A skin lesion imaged with a dermatoscope:
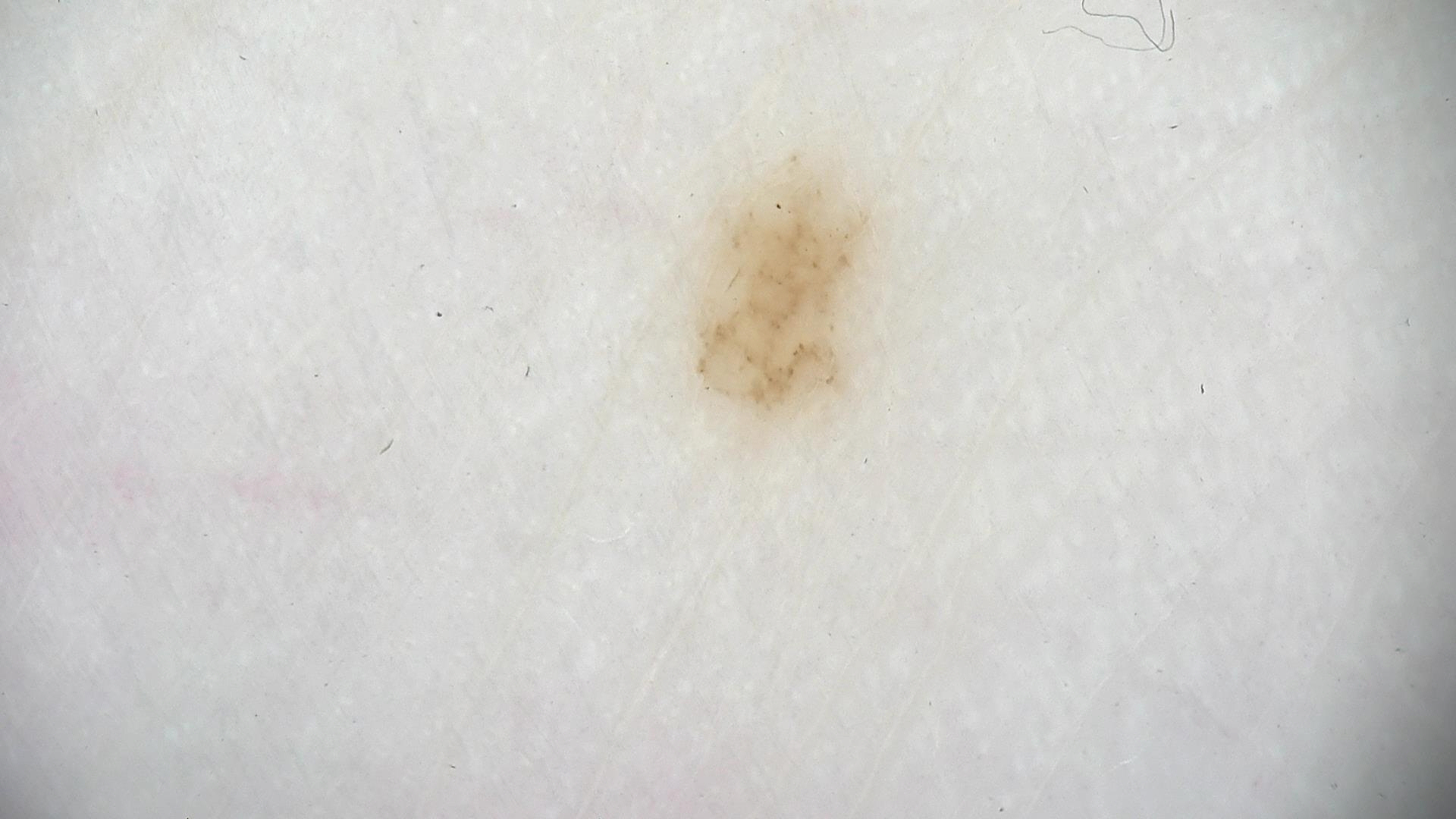class = dysplastic junctional nevus (expert consensus).